A dermoscopy image of a skin lesion. The patient says their skin reddens with sun exposure — 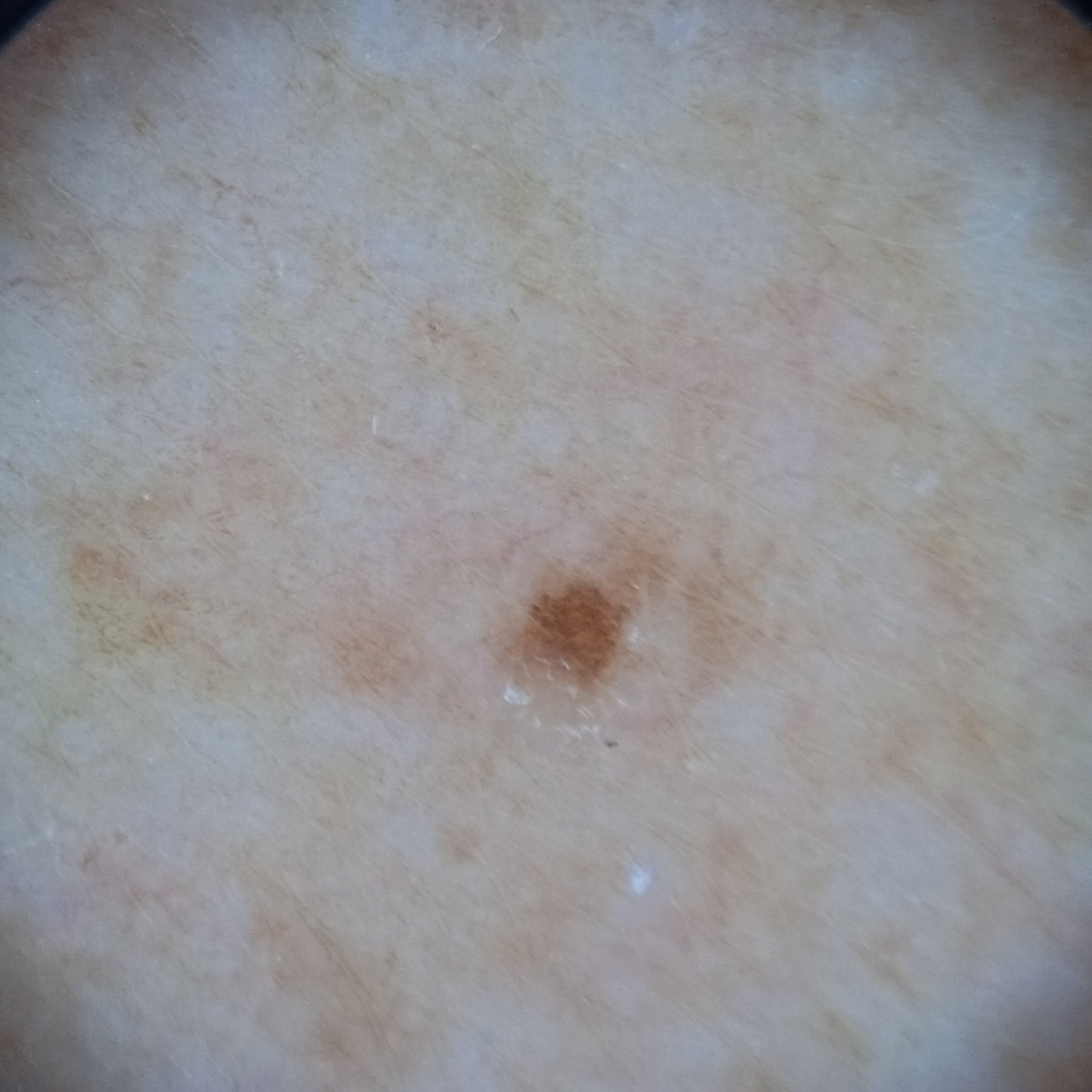The lesion is on an arm.
Measuring roughly 1.3 mm.
Reviewed by four dermatologists, the consensus diagnosis was a melanocytic nevus; the reviewers' opinions were divided; diagnostic confidence was moderate.